Skin tone: Fitzpatrick phototype II · female contributor, age 30–39 · an image taken at a distance · symptoms reported: burning and itching · the patient described the issue as a rash · reported duration is less than one week — 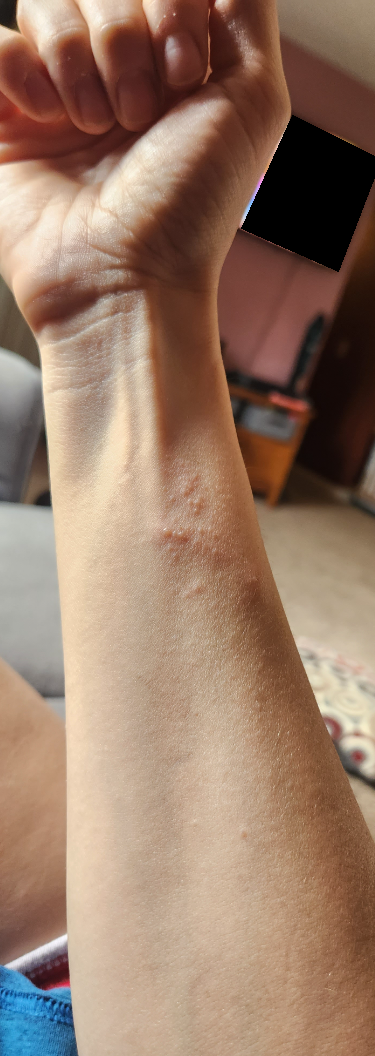On photographic review by a dermatologist, Koebner phenomenon (55%); Molluscum Contagiosum (27%); Viral Exanthem (18%).